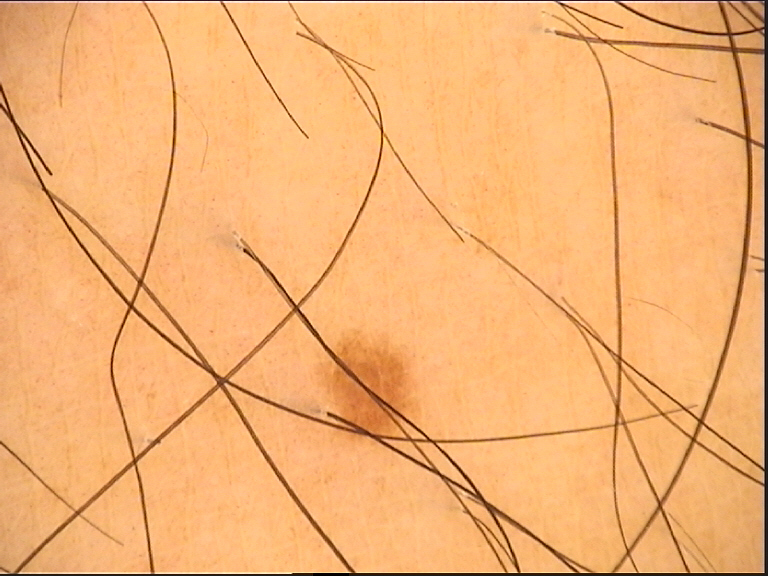A dermoscopic close-up of a skin lesion. Classified as a banal lesion — a junctional nevus.